Skin tone: Fitzpatrick II; non-clinician graders estimated a Monk Skin Tone of 2. The lesion involves the leg. An image taken at an angle. Symptoms reported: itching. Present for about one day.
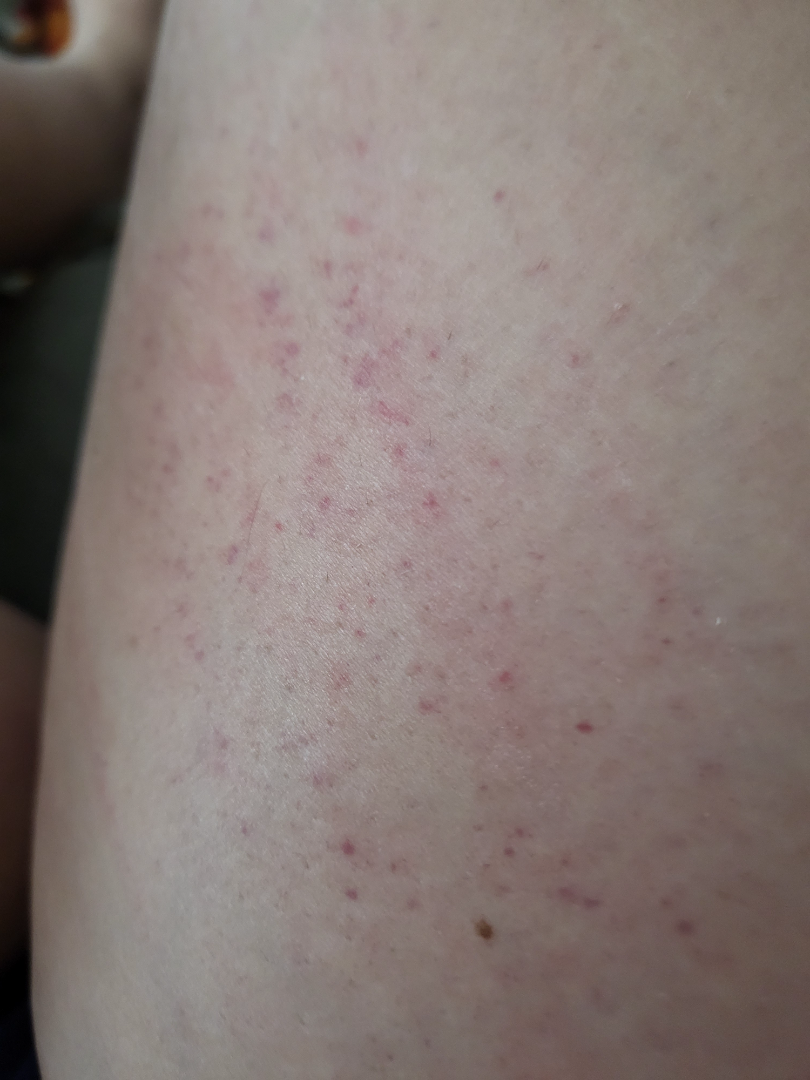Findings:
– assessment: the leading consideration is Traumatic petechiae